The chart records prior skin cancer (patient or family), tobacco use, and prior malignancy (patient or family). A female subject in their 60s. A clinical close-up photograph of a skin lesion — 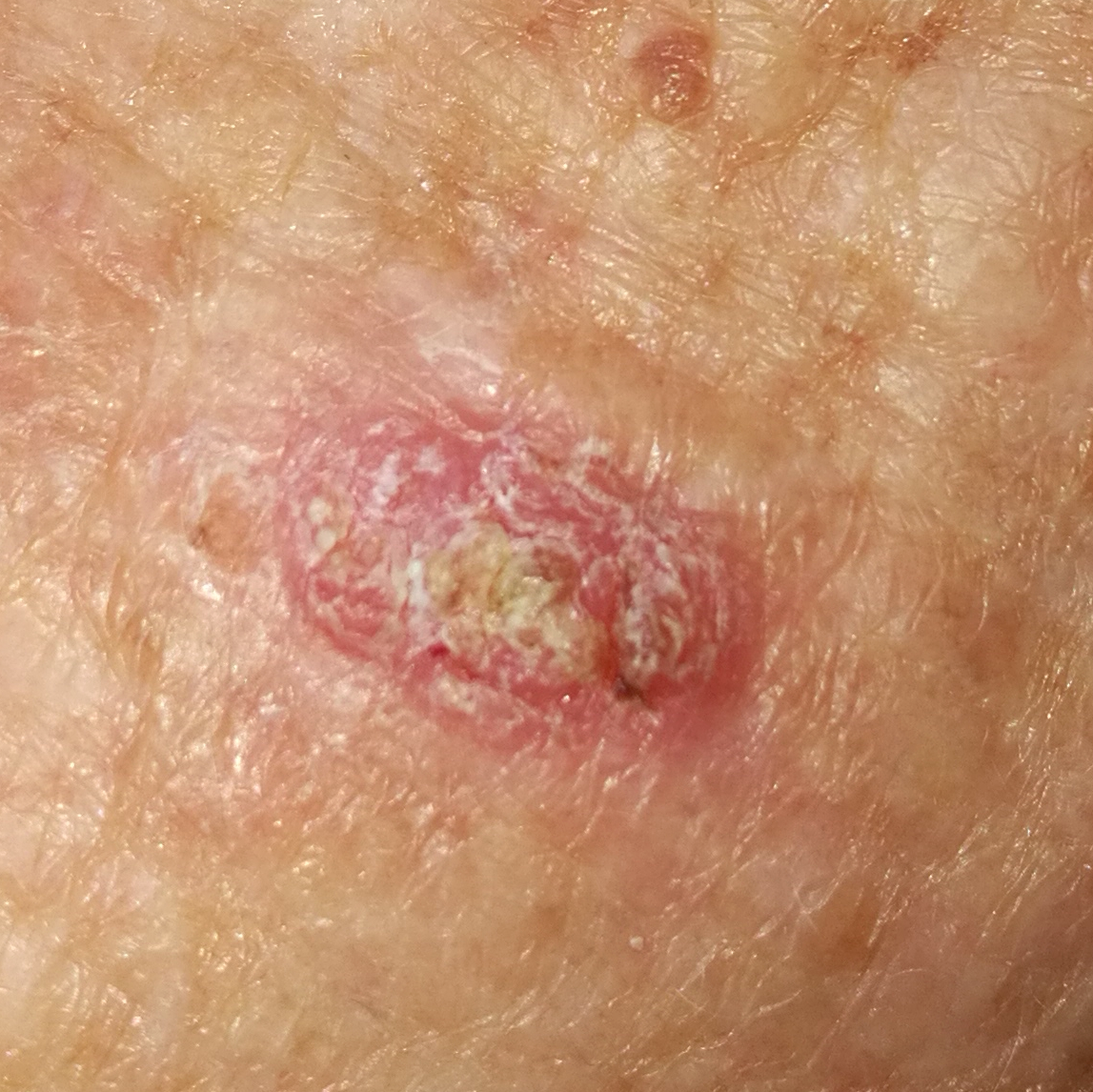Clinical context:
The lesion measures 11 × 6 mm. Per patient report, the lesion has bled, is elevated, itches, and has grown.
Diagnosis:
Histopathological examination showed a squamous cell carcinoma.